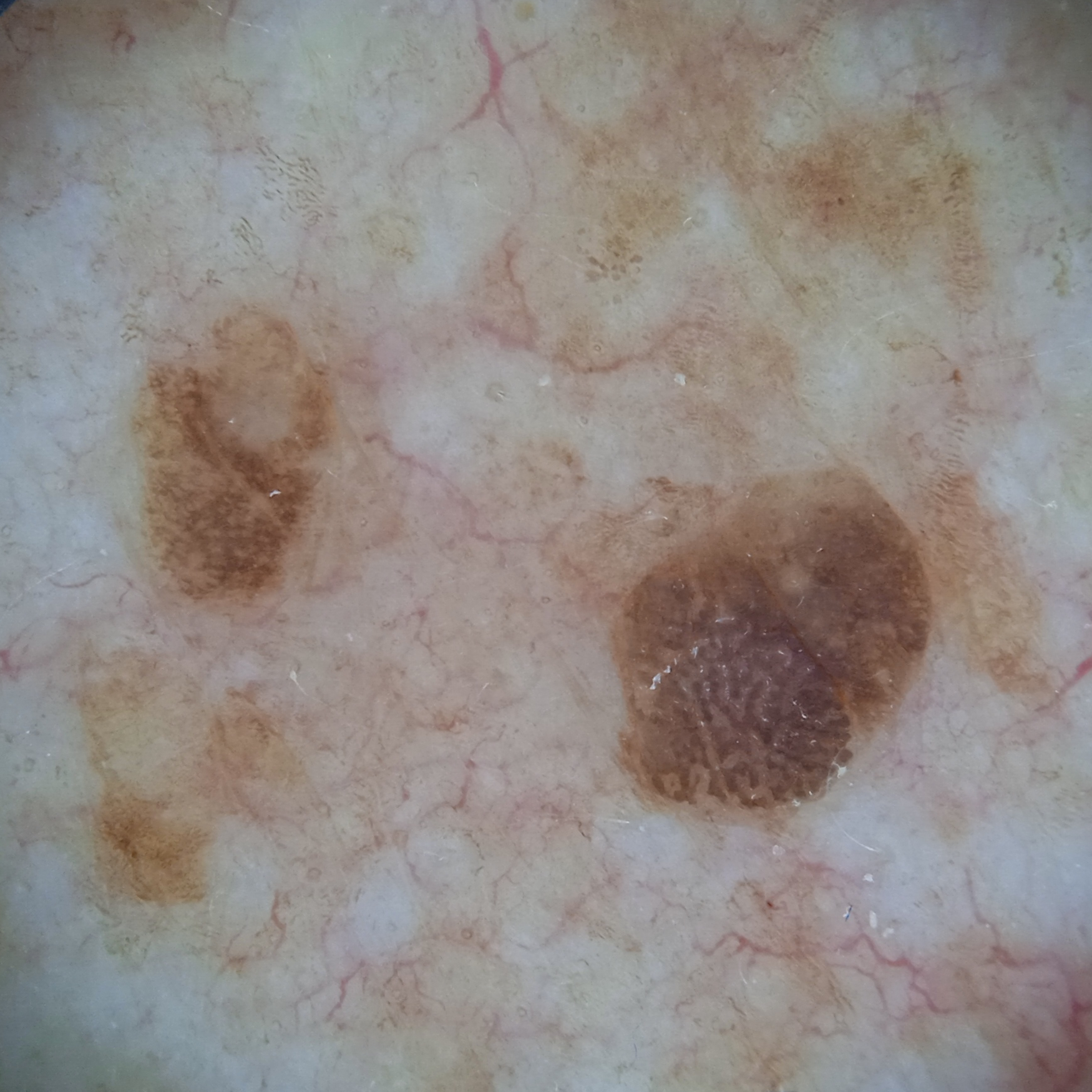Findings:
The patient says their skin tans without first burning. A dermatoscopic image of a skin lesion. The patient describes having few moles overall. By self-report, a personal history of cancer. A female subject 84 years of age. Collected as part of a research study, without a referral diagnosis. The lesion is located on the torso. Measuring roughly 4.6 mm.
Conclusion:
The diagnostic impression was a seborrheic keratosis.